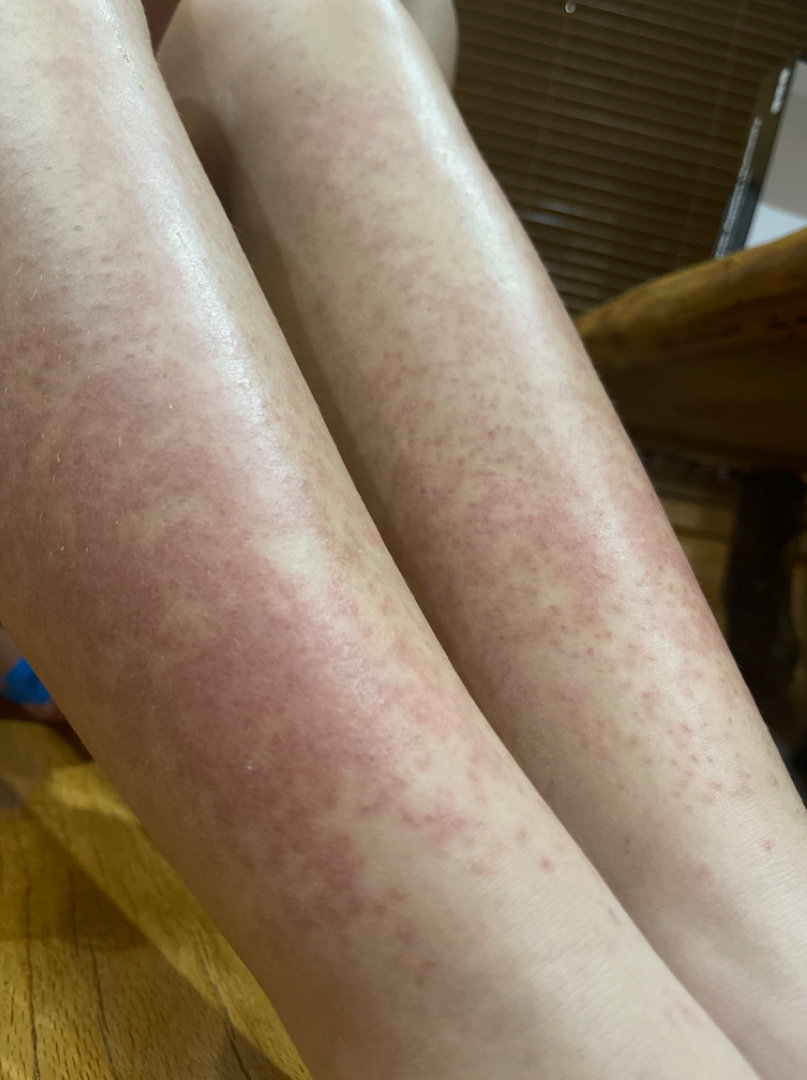differential diagnosis: most consistent with Drug Rash; with consideration of Viral Exanthem; less likely is Leukocytoclastic Vasculitis.